A close-up photograph — 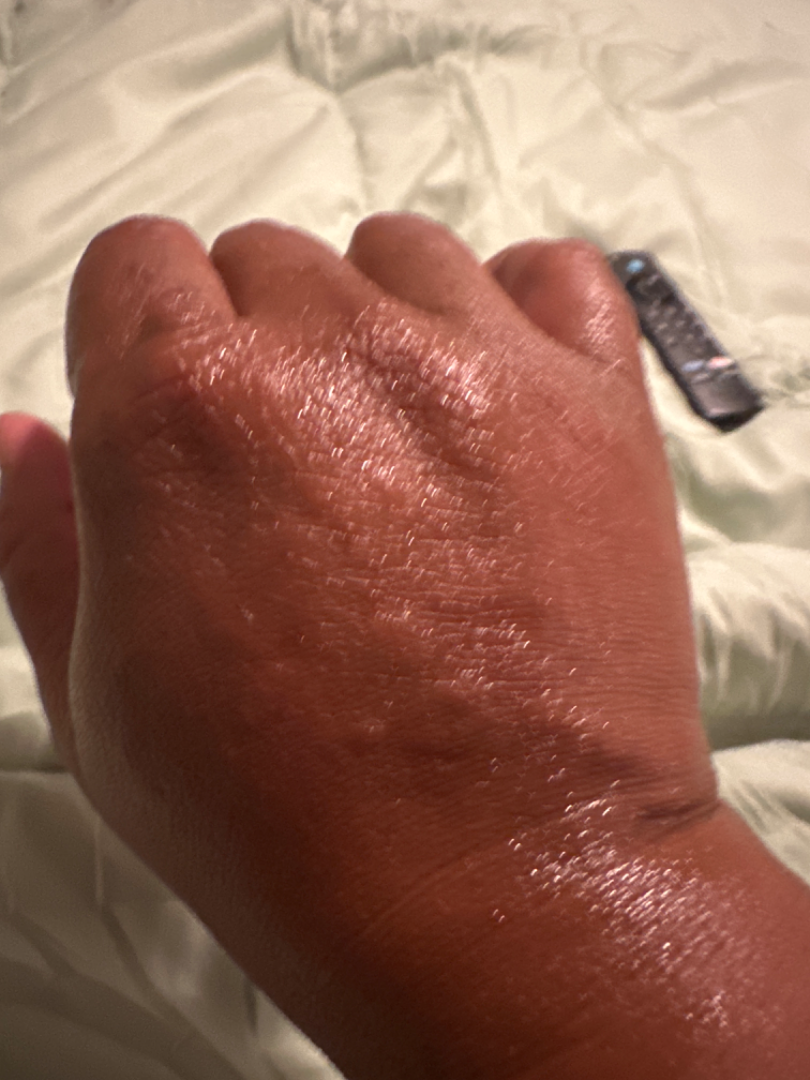<summary>
<differential>
  <leading>Urticaria</leading>
</differential>
</summary>